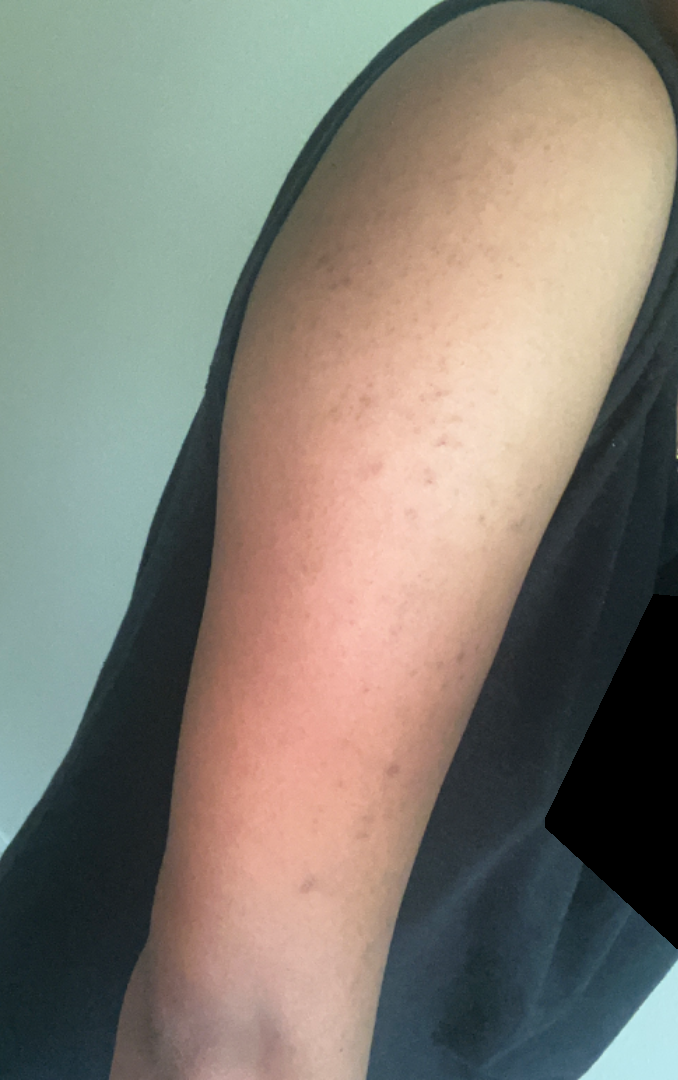reported symptoms — itching and bothersome appearance; texture — raised or bumpy; patient's own categorization — acne; affected area — arm, back of the hand and back of the torso; history — more than five years; associated systemic symptoms — none reported; contributor — female, age 18–29; image framing — at a distance; impression — consistent with Keratosis pilaris.